A patient 40 years old · a clinical photograph of a skin lesion — 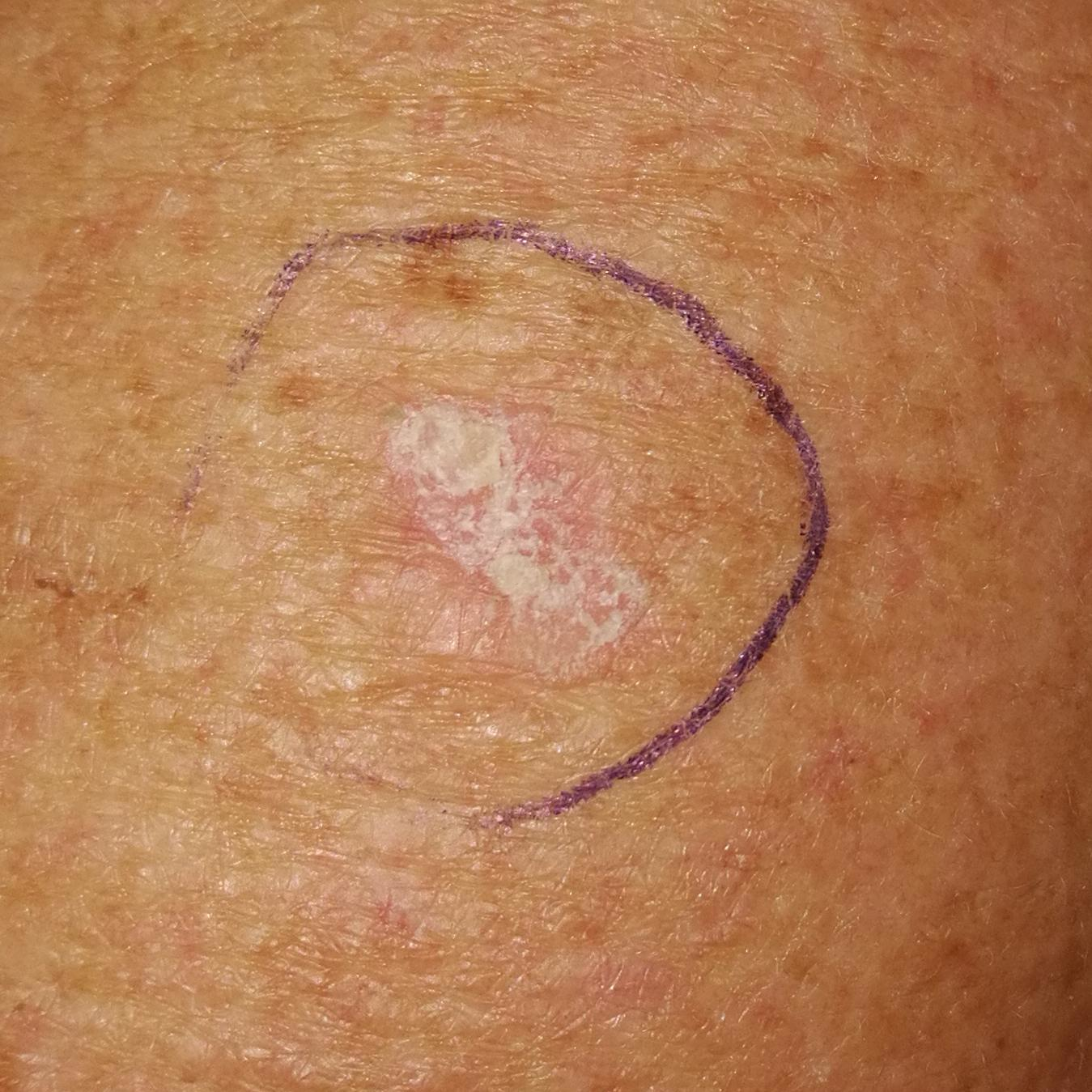The lesion was found on a forearm. The patient describes that the lesion itches, but is not elevated and has not grown. Consistent with a premalignant lesion — an actinic keratosis.